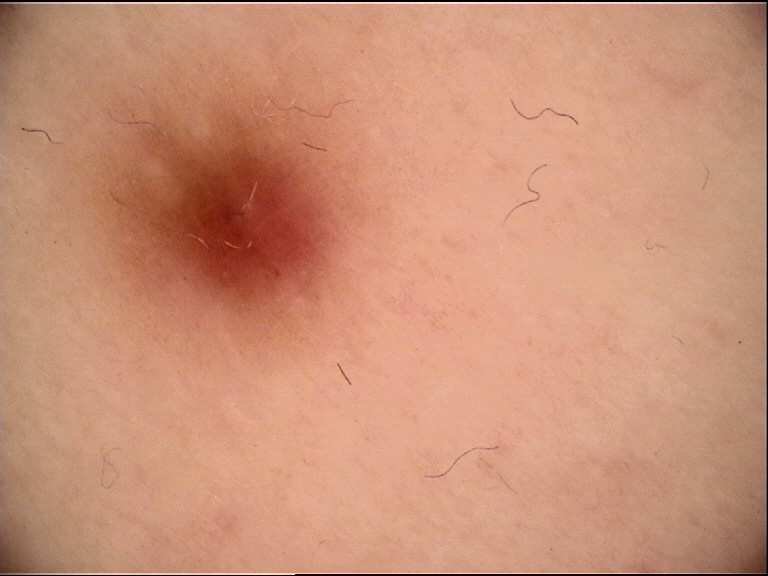<case>
<image>dermatoscopy</image>
<lesion_type>
<main_class>fibro-histiocytic</main_class>
</lesion_type>
<diagnosis>
<name>dermatofibroma</name>
<code>df</code>
<malignancy>benign</malignancy>
<super_class>non-melanocytic</super_class>
<confirmation>expert consensus</confirmation>
</diagnosis>
</case>